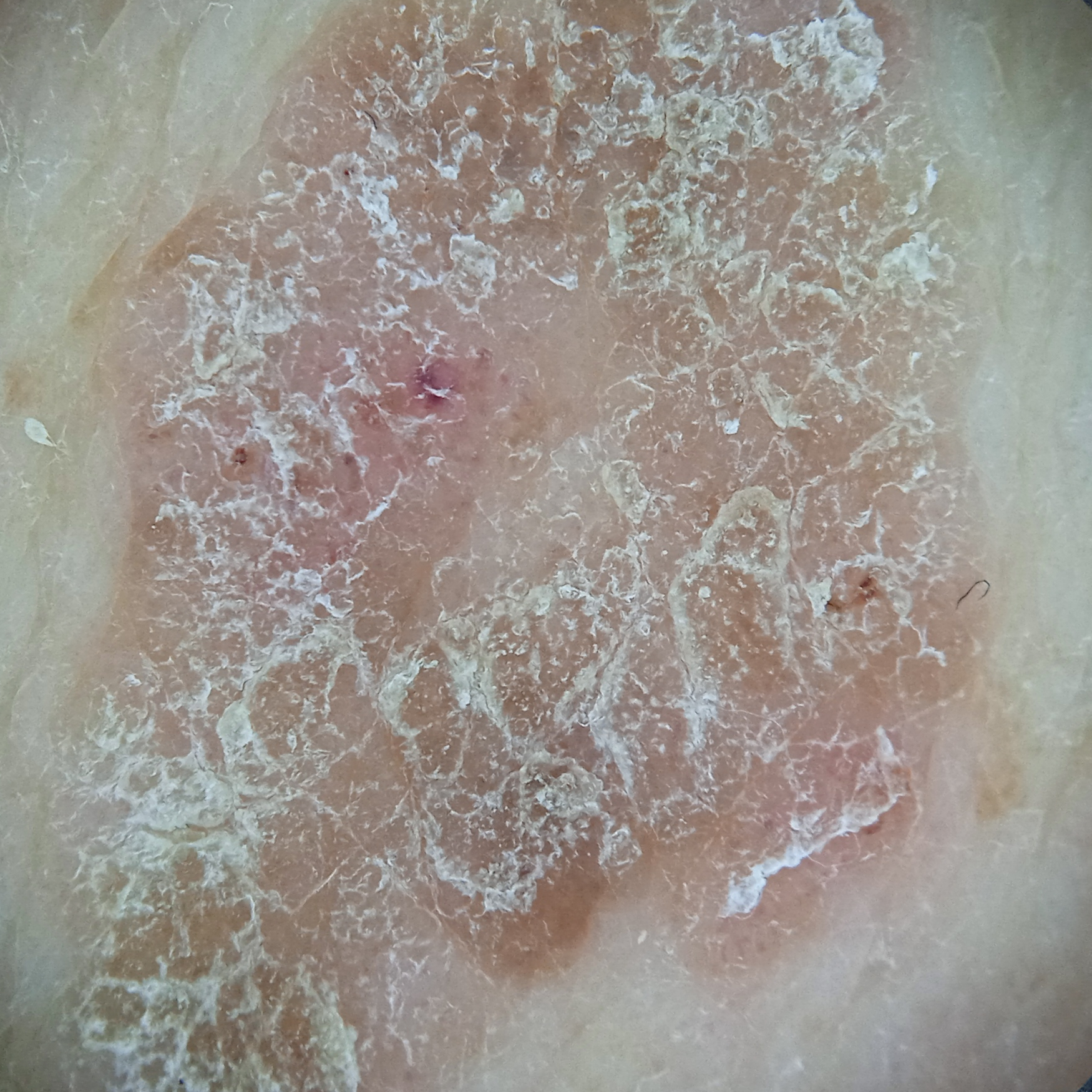referral context: research study (no referral diagnosis) | sun reaction: skin reddens with sun exposure | relevant history: a personal history of cancer | subject: male, 72 years old | nevus count: few melanocytic nevi overall | image: dermoscopy | anatomic site: the back | size: 16.5 mm | diagnostic label: seborrheic keratosis (dermatologist consensus).